The photograph was taken at an angle:
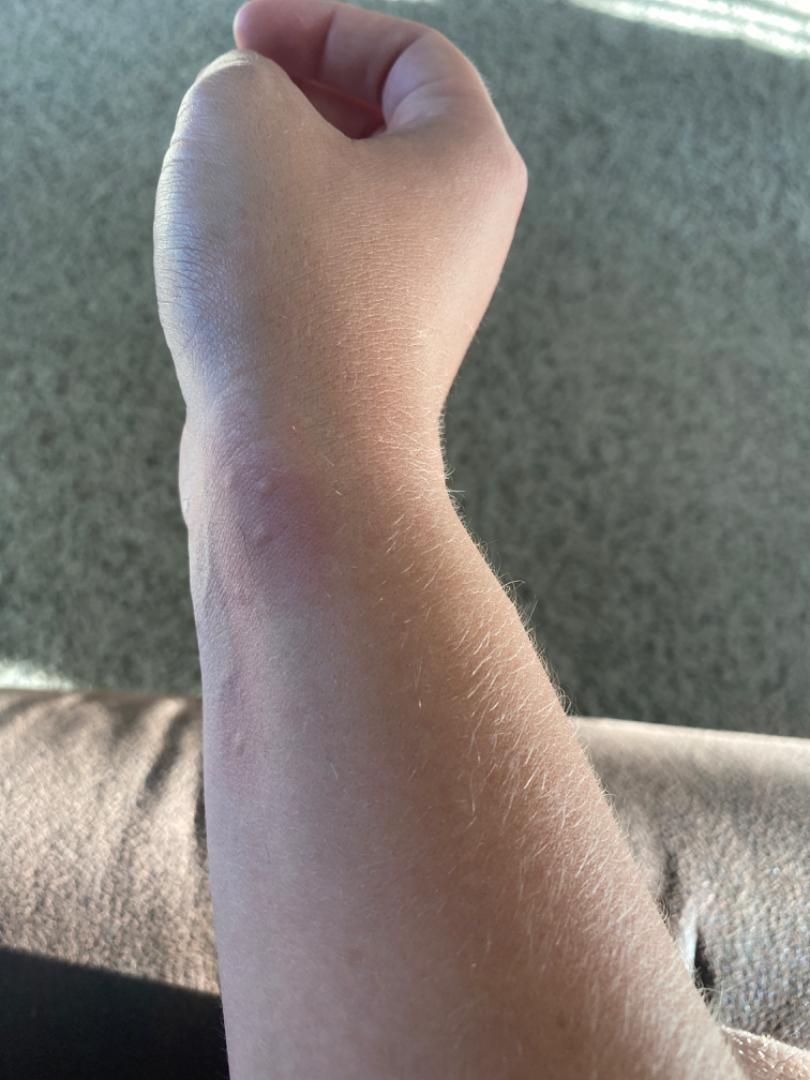One reviewing dermatologist: most consistent with Insect Bite; also raised was Urticaria.